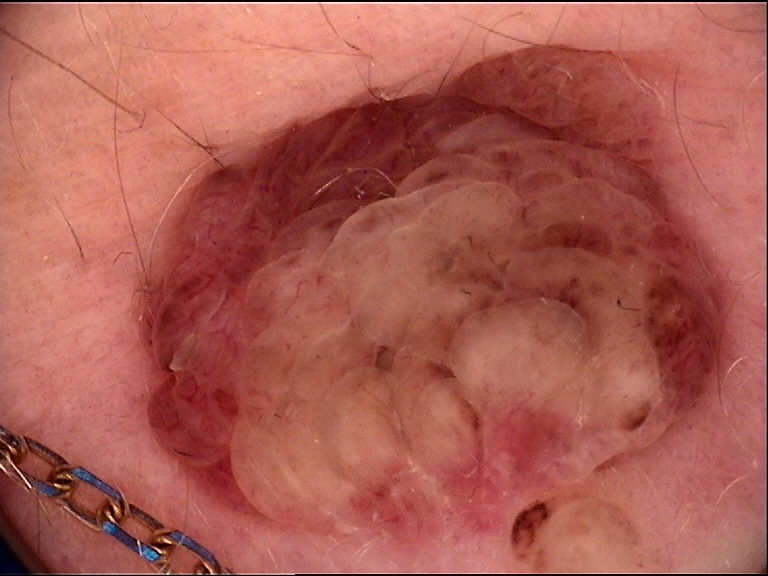The diagnostic label was a dermal nevus.